A dermoscopic image of a skin lesion.
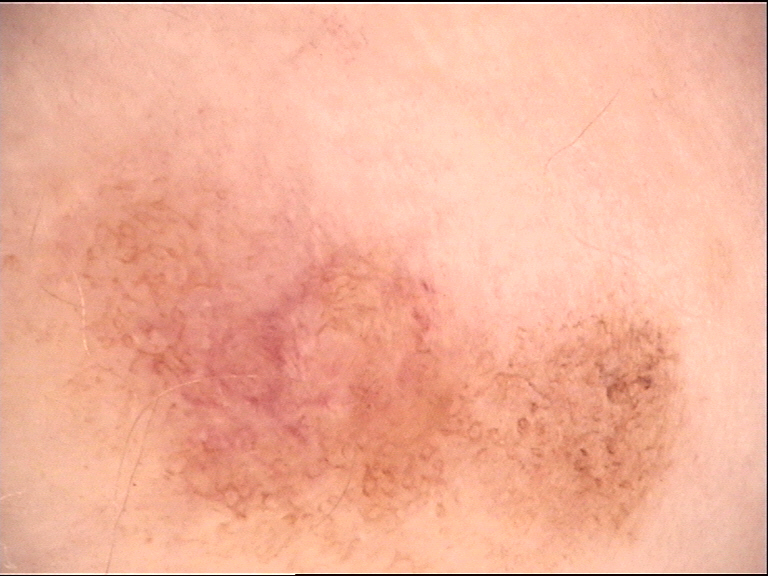<case>
<diagnosis>
<name>dysplastic junctional nevus</name>
<code>jd</code>
<malignancy>benign</malignancy>
<super_class>melanocytic</super_class>
<confirmation>expert consensus</confirmation>
</diagnosis>
</case>